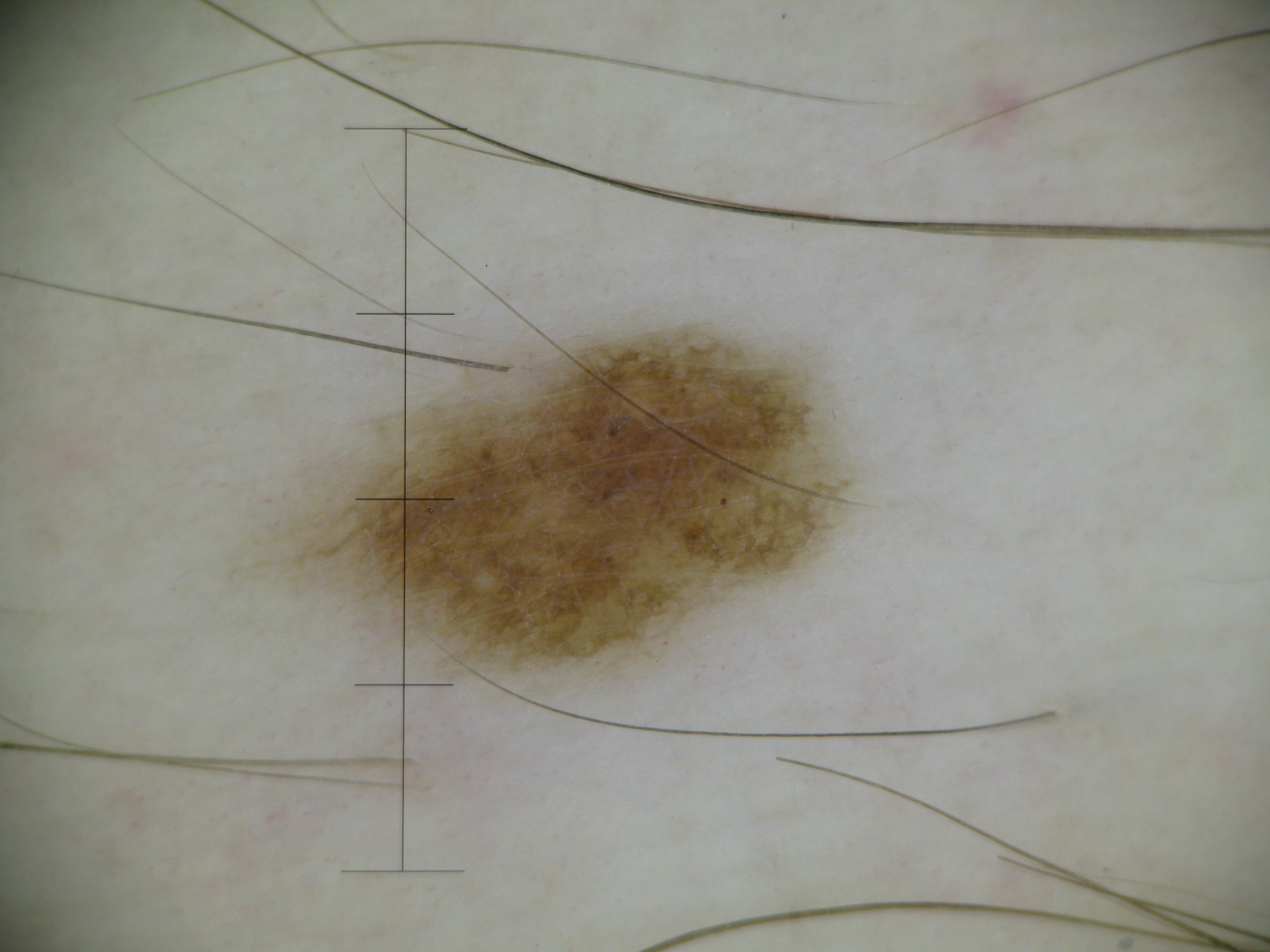Findings:
- imaging · dermoscopy
- diagnostic label · dysplastic junctional nevus (expert consensus)